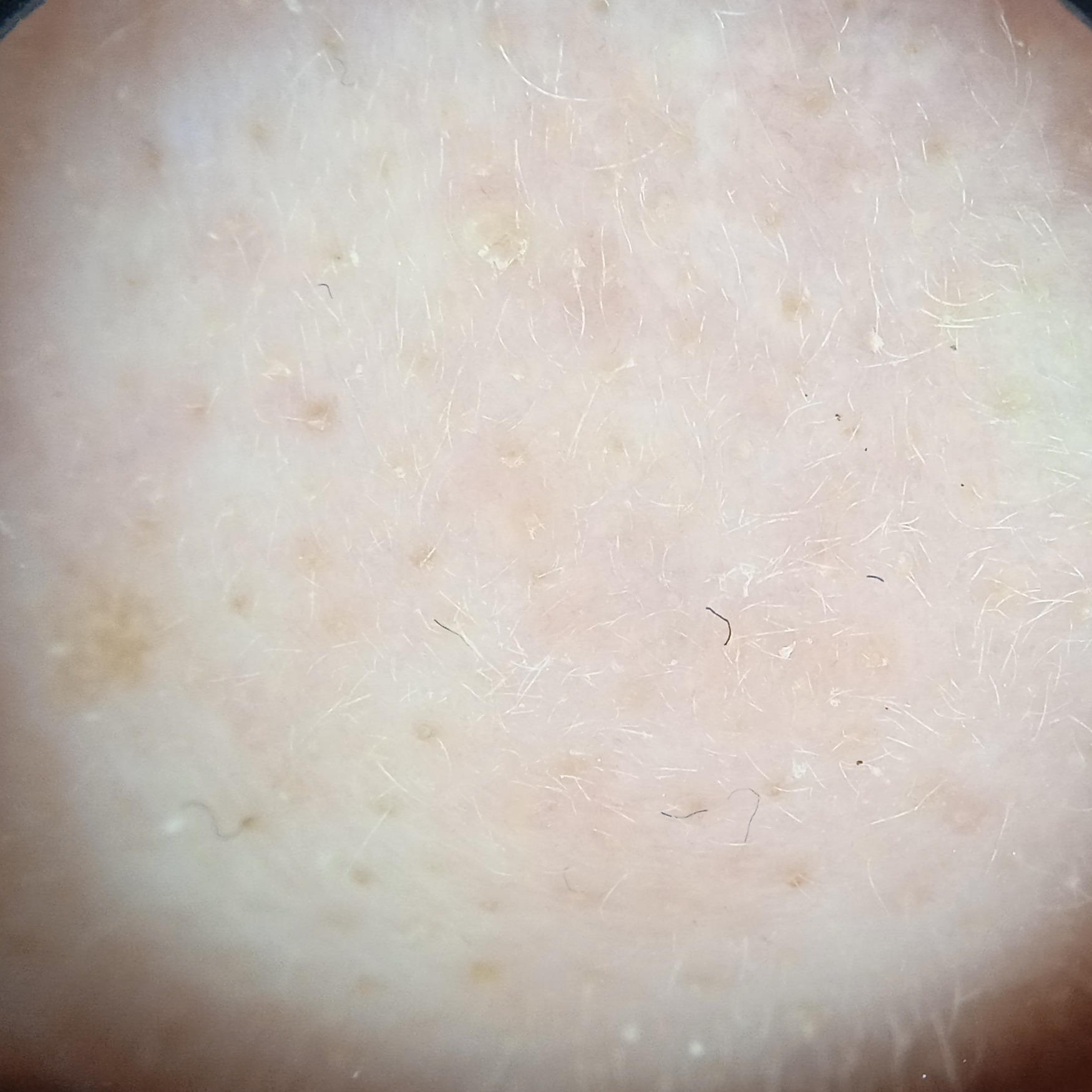Findings: A dermoscopic image of a skin lesion. The referring clinician suspected basal cell carcinoma. The lesion is on the face. Impression: The dermatologists' assessment was an actinic keratosis.